A clinical photograph showing a skin lesion:
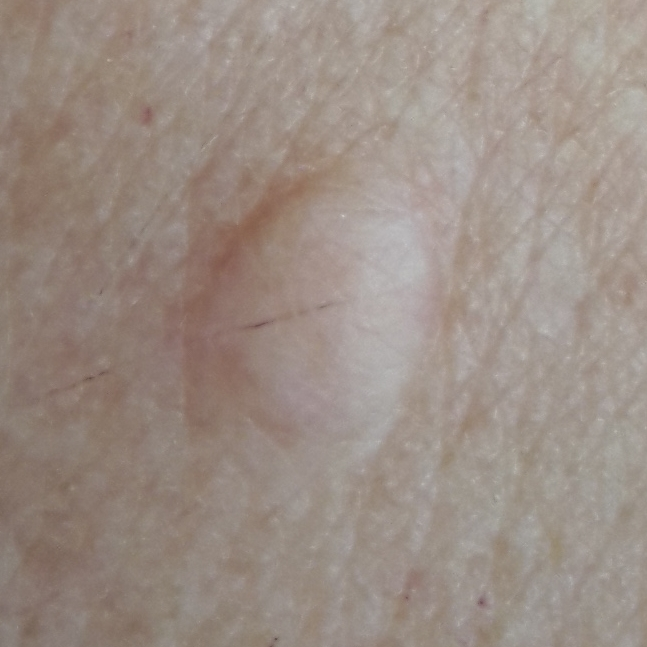lesion_location: the chest
symptoms:
  present:
    - elevation
    - itching
    - growth
diagnosis:
  name: nevus
  code: NEV
  malignancy: benign
  confirmation: clinical consensus